This is a dermoscopic photograph of a skin lesion · the patient is a male aged 58 to 62:
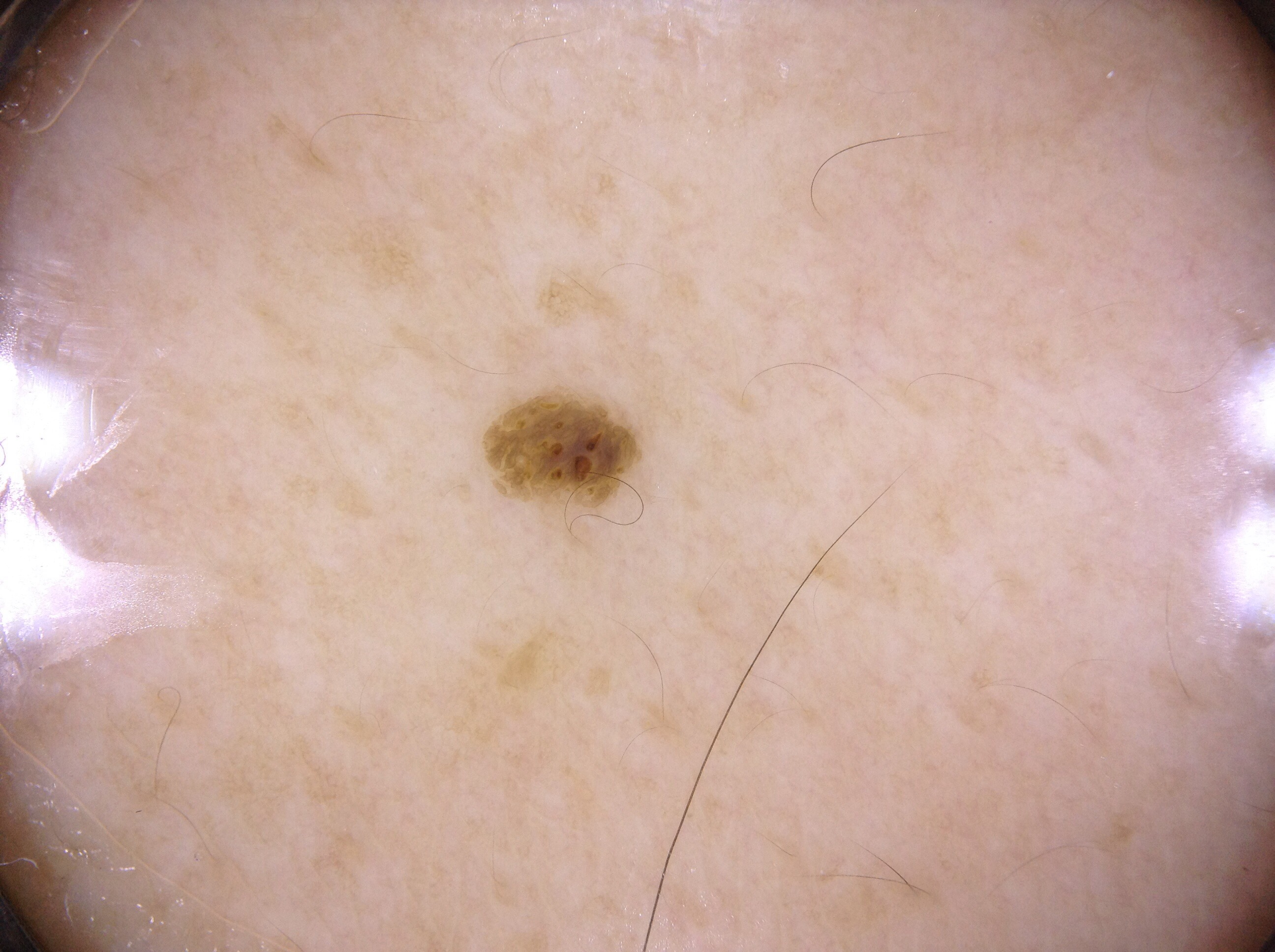Q: Which assessed dermoscopic features were absent?
A: pigment network, milia-like cysts, streaks, and negative network
Q: Where is the lesion located?
A: 498 402 627 498
Q: What is the diagnosis?
A: a seborrheic keratosis, a benign skin lesion